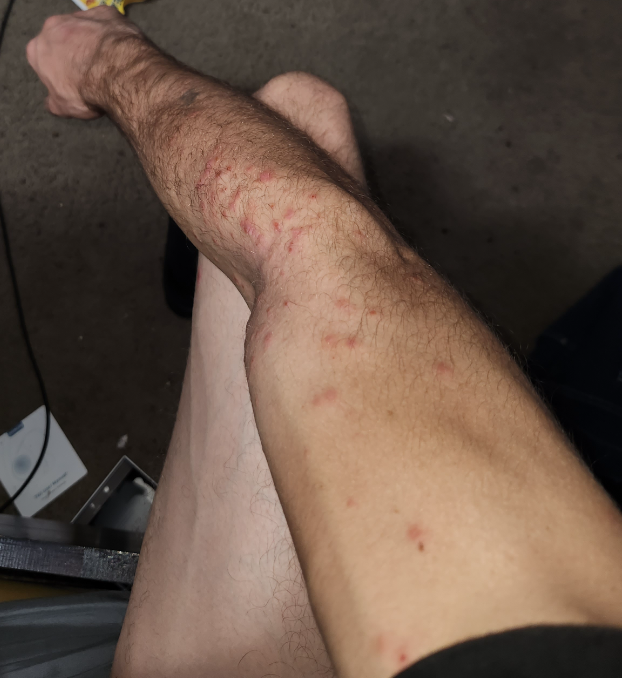Q: Patient demographics?
A: male, age 18–29
Q: What is the framing?
A: at a distance
Q: What is the affected area?
A: arm
Q: What conditions are considered?
A: most consistent with Viral Exanthem; an alternative is Scabies; a more distant consideration is Eczema